Imaged for a research study, with no referral diagnosis recorded · the patient describes having a moderate number of moles · dermoscopy of a skin lesion · the patient says their skin reddens painfully with sun exposure.
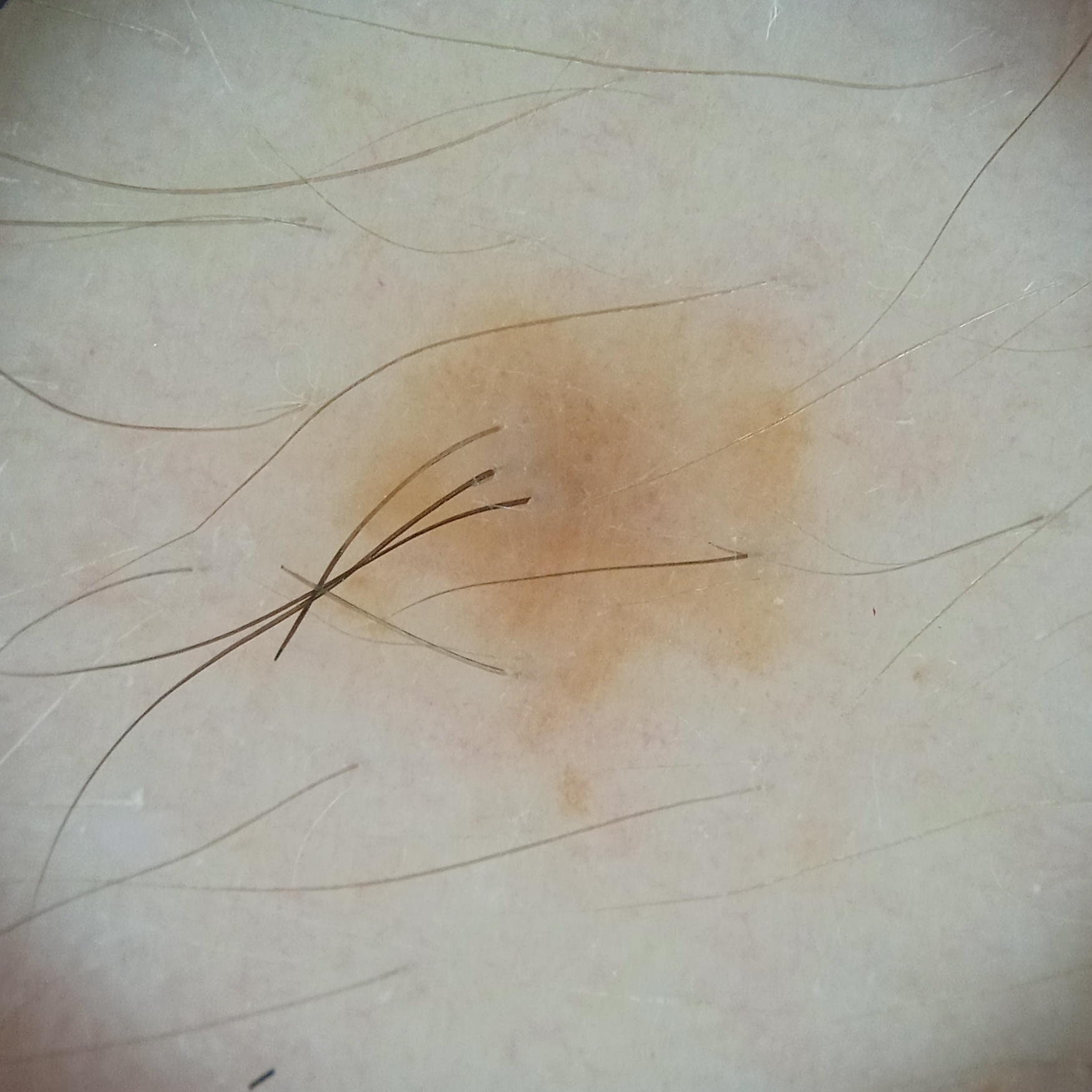The lesion is on an arm.
The dermatologists' assessment was a melanocytic nevus.